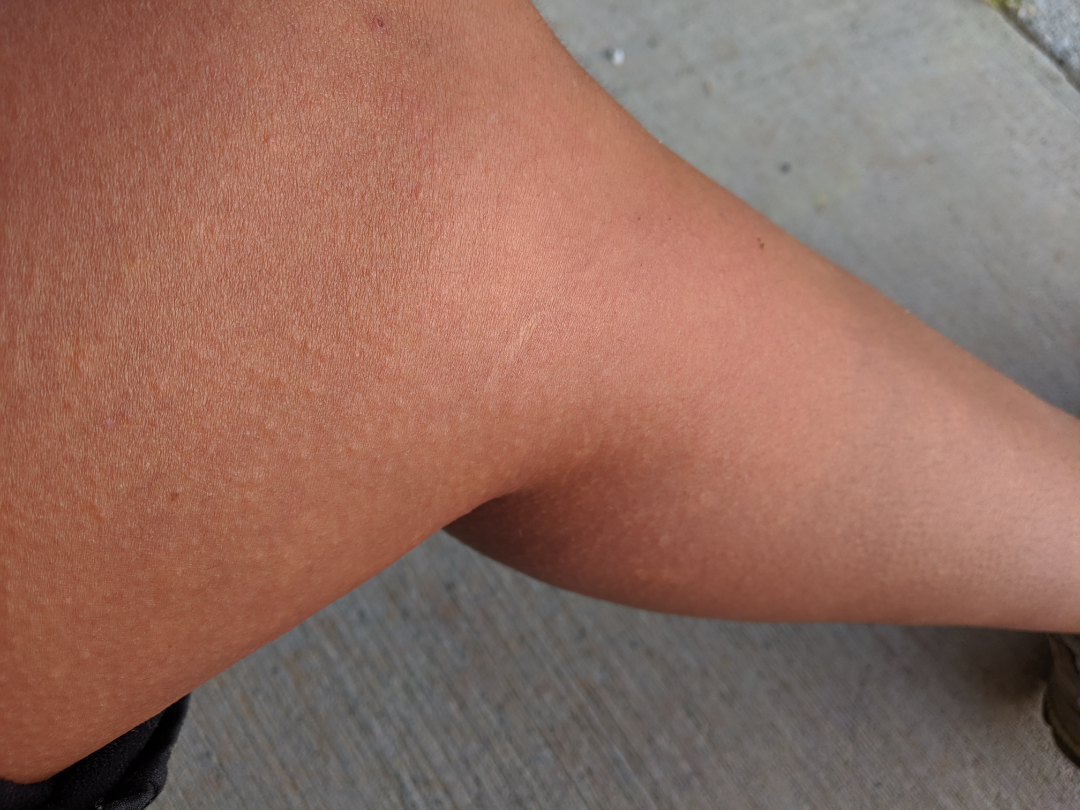Findings: The condition could not be reliably identified from the image. Background: The affected area is the leg. Close-up view.